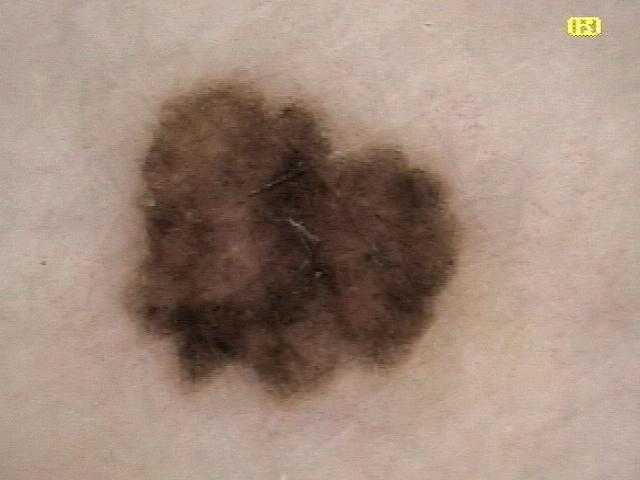The patient was assessed as FST II. A contact-polarized dermoscopy image of a skin lesion. A female patient approximately 65 years of age. The chart records melanoma in a first-degree relative. Located on a lower extremity. Histopathological examination showed a benign, melanocytic lesion — a nevus.